This is a close-up image, the contributor reports the condition has been present for one to four weeks, Fitzpatrick phototype IV; human graders estimated MST 3–4, located on the leg — 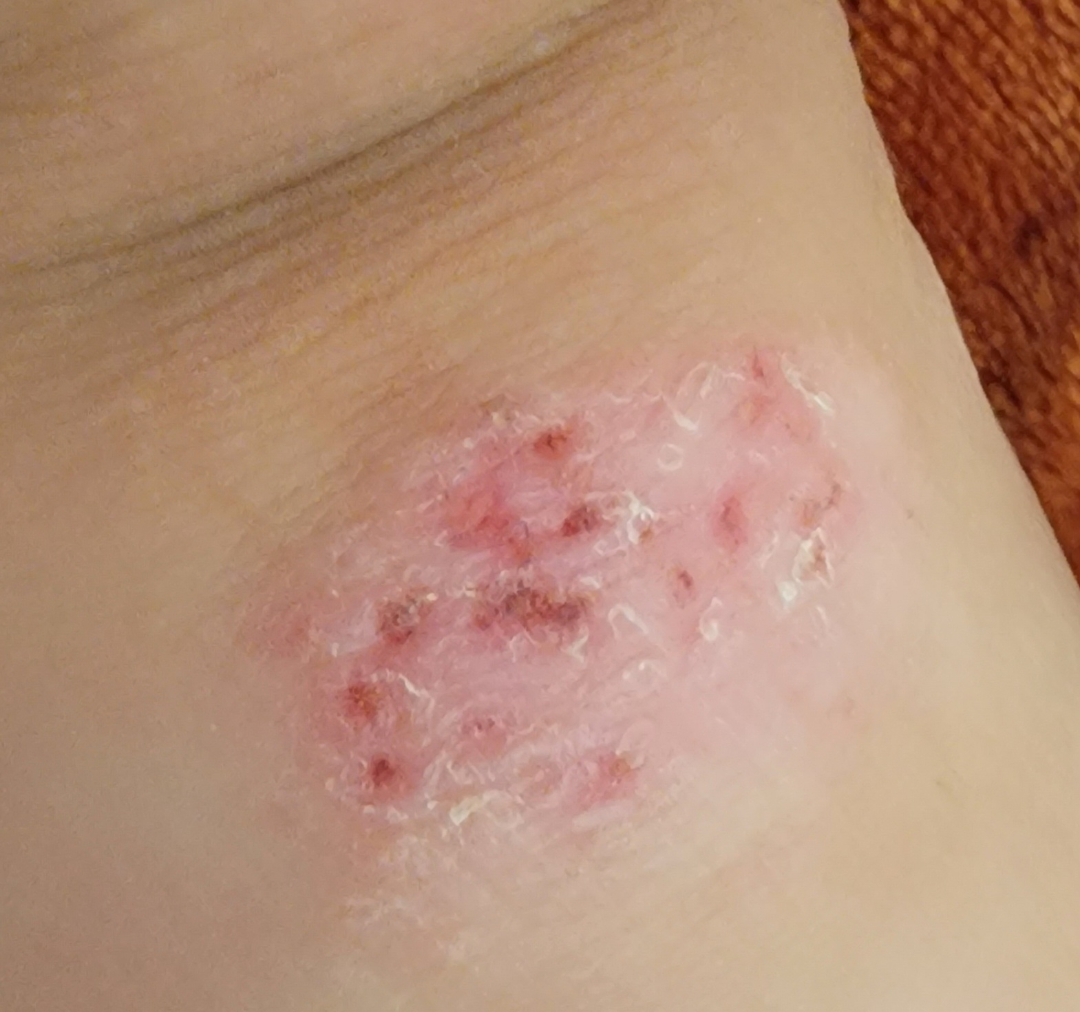The image was not sufficient for the reviewer to characterize the skin condition.